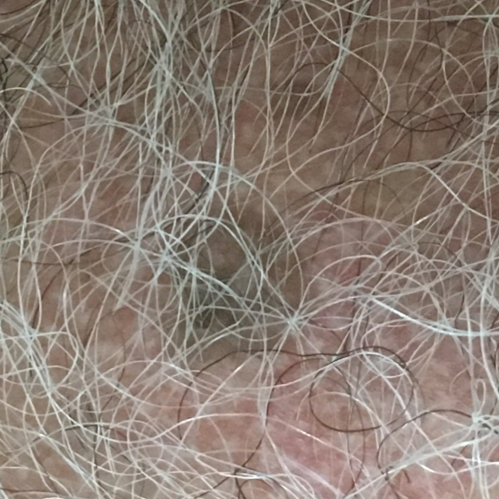anatomic site: the chest; symptoms: itching, elevation / no growth; impression: seborrheic keratosis (clinical consensus).